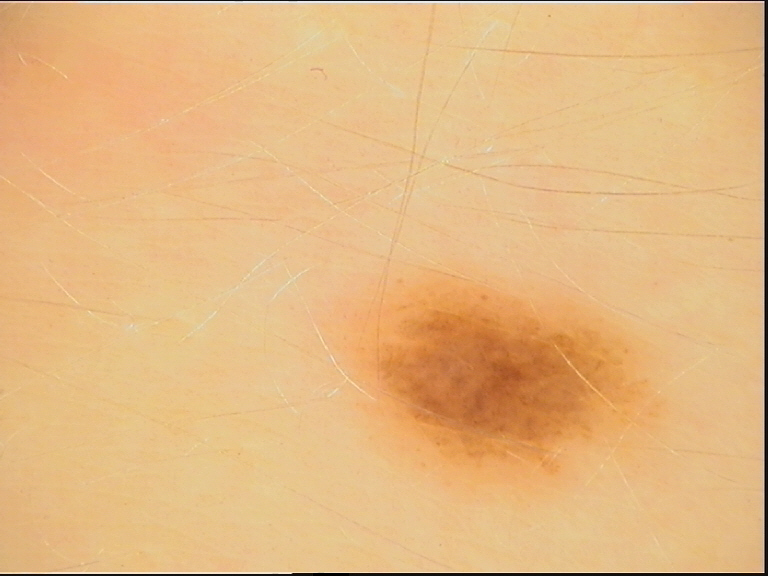The diagnostic label was a dysplastic junctional nevus.